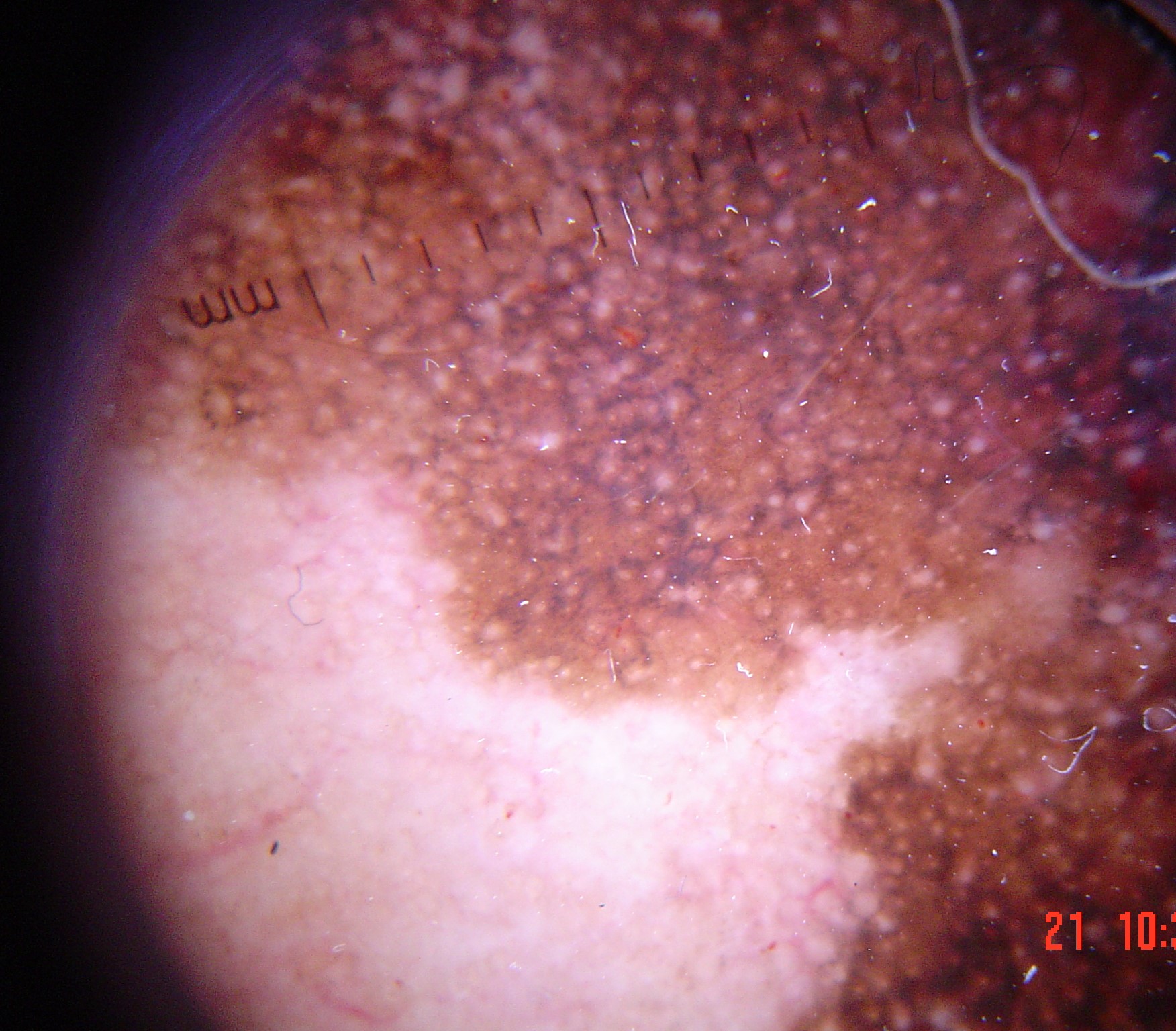Diagnosis:
Biopsy-confirmed as a lentigo maligna.